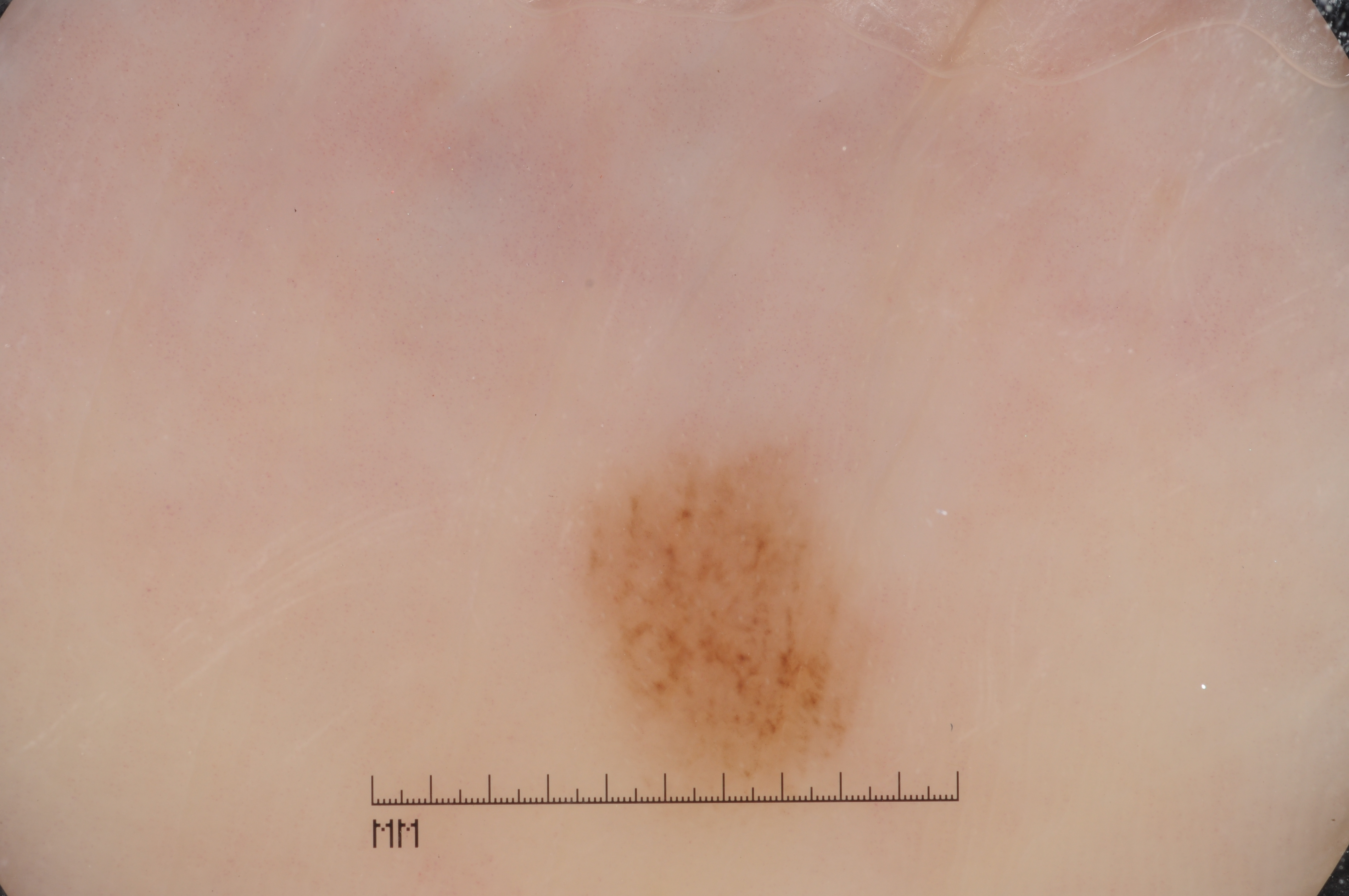{
  "patient": {
    "sex": "female",
    "age_approx": 60
  },
  "image": {
    "modality": "dermoscopy"
  },
  "dermoscopic_features": {
    "present": [],
    "absent": [
      "pigment network",
      "negative network",
      "milia-like cysts",
      "streaks"
    ]
  },
  "lesion_location": {
    "bbox_xyxy": [
      569,
      434,
      885,
      812
    ]
  },
  "lesion_extent": "small",
  "diagnosis": {
    "name": "melanocytic nevus",
    "malignancy": "benign",
    "lineage": "melanocytic",
    "provenance": "clinical"
  }
}